A skin lesion imaged with a dermatoscope — 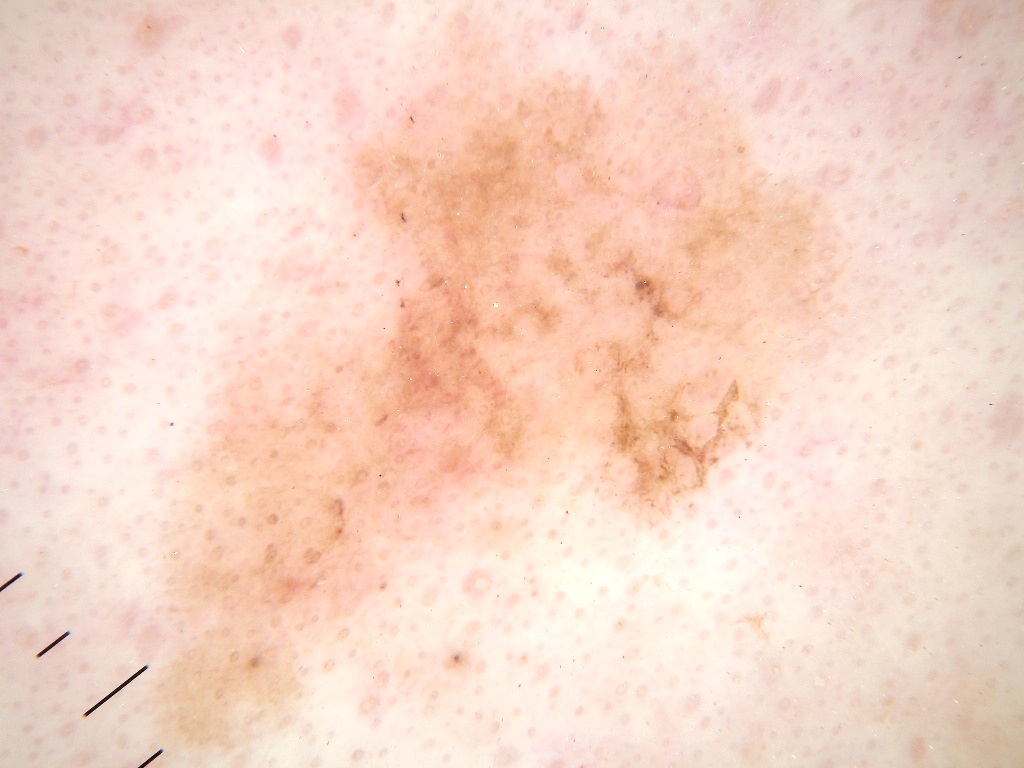Dermoscopic examination shows no negative network, streaks, milia-like cysts, globules, or pigment network.
The lesion covers approximately 43% of the dermoscopic field.
In (x1, y1, x2, y2) order, the lesion is located at <bbox>134, 33, 875, 766</bbox>.
Biopsy-confirmed as a melanoma.